The chart records prior skin cancer (patient or family). A male patient 61 years old. The patient is Fitzpatrick skin type III. A clinical photo of a skin lesion taken with a smartphone: 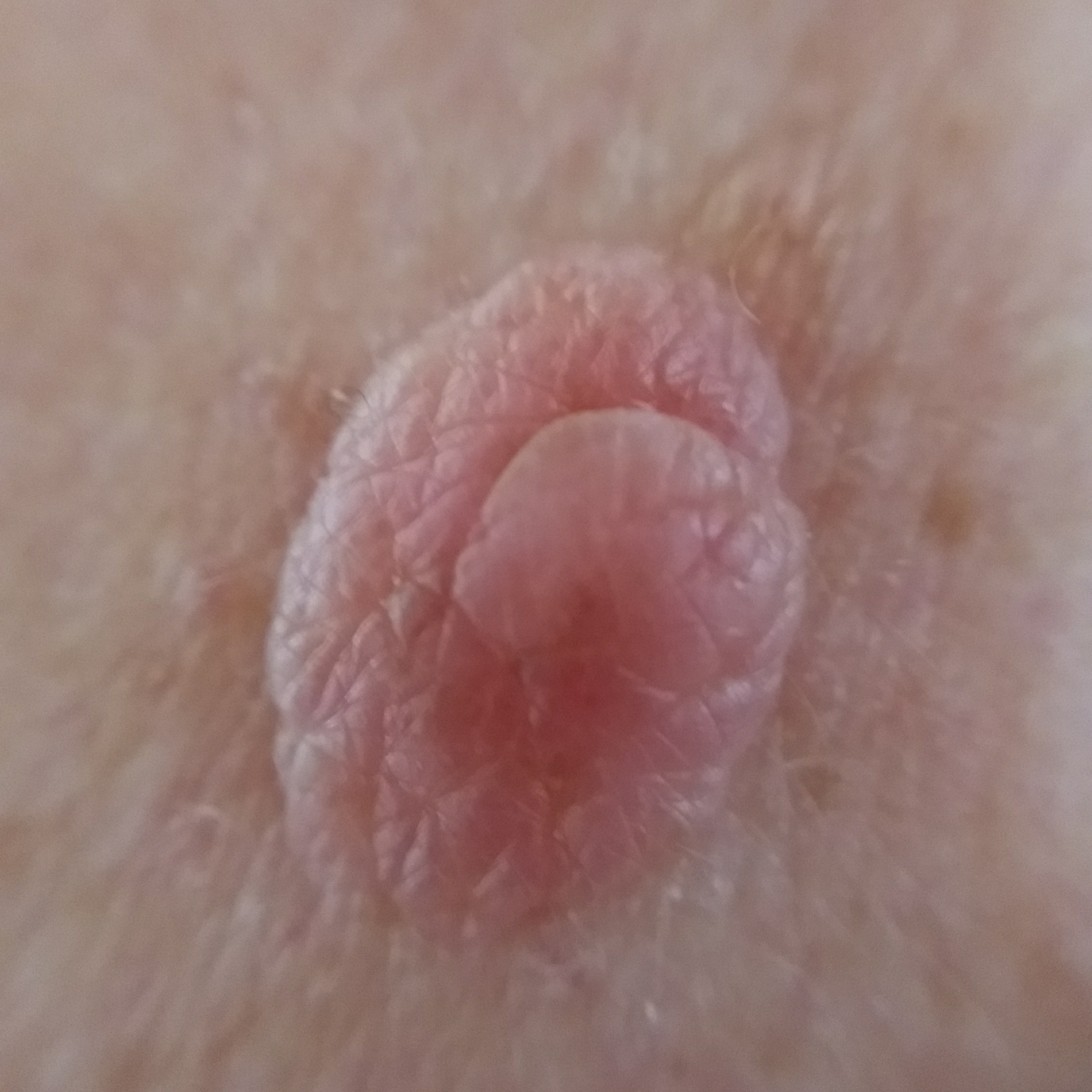size=2 × 2 mm; symptoms=elevation; diagnosis=nevus (clinical consensus).